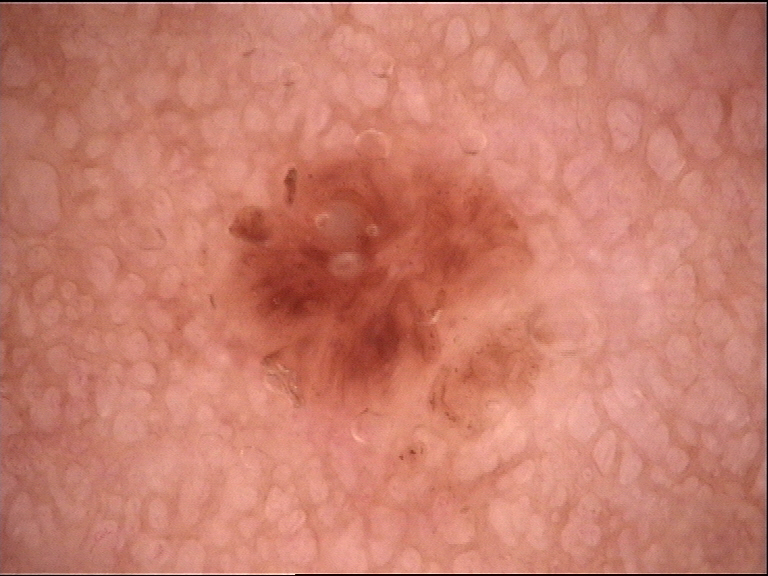Dermoscopy of a skin lesion. Diagnosed as a dermal nevus.